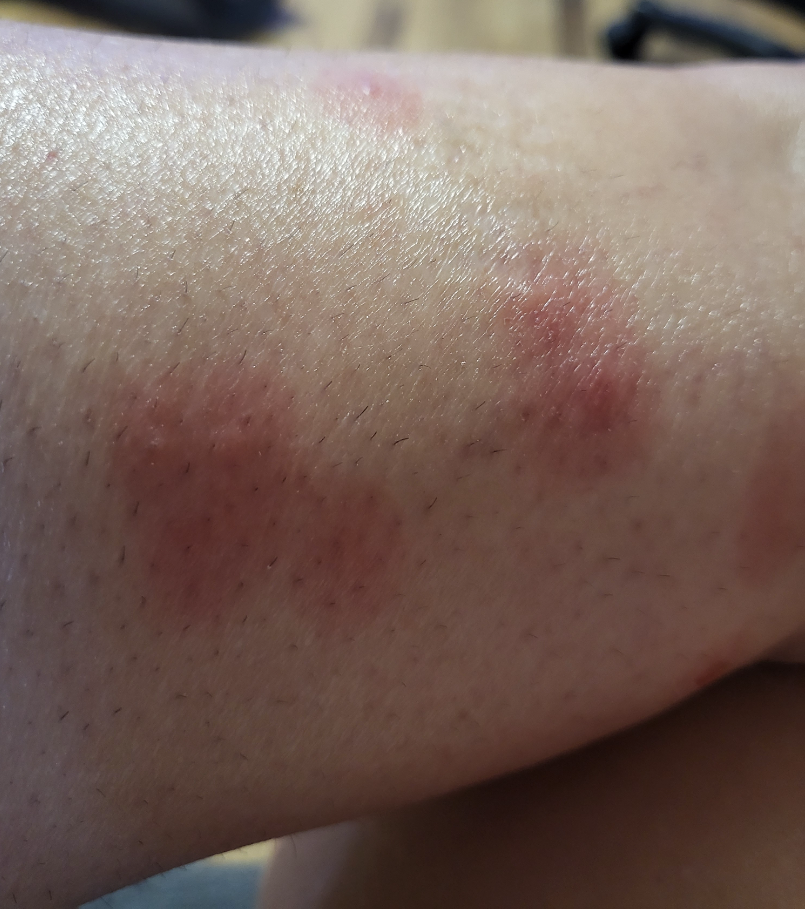diagnostic considerations = one reviewing dermatologist: consistent with Insect Bite.